The patient described the issue as a rash. Located on the leg, front of the torso, arm, top or side of the foot and head or neck. Reported lesion symptoms include itching, pain, bothersome appearance, bleeding, burning and enlargement. Associated systemic symptoms include fatigue and fever. Texture is reported as raised or bumpy, rough or flaky and fluid-filled. The patient notes the condition has been present for one to three months. Female contributor, age 50–59. This image was taken at an angle: 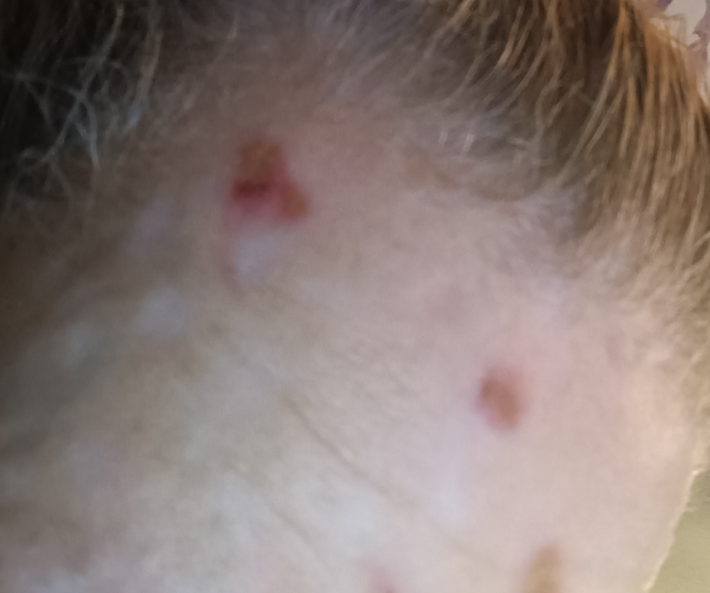diagnostic considerations: favoring Acne